The photograph is a close-up of the affected area. Reported duration is about one day. The lesion is associated with itching. The patient considered this a rash. The front of the torso is involved. The contributor notes the lesion is raised or bumpy.
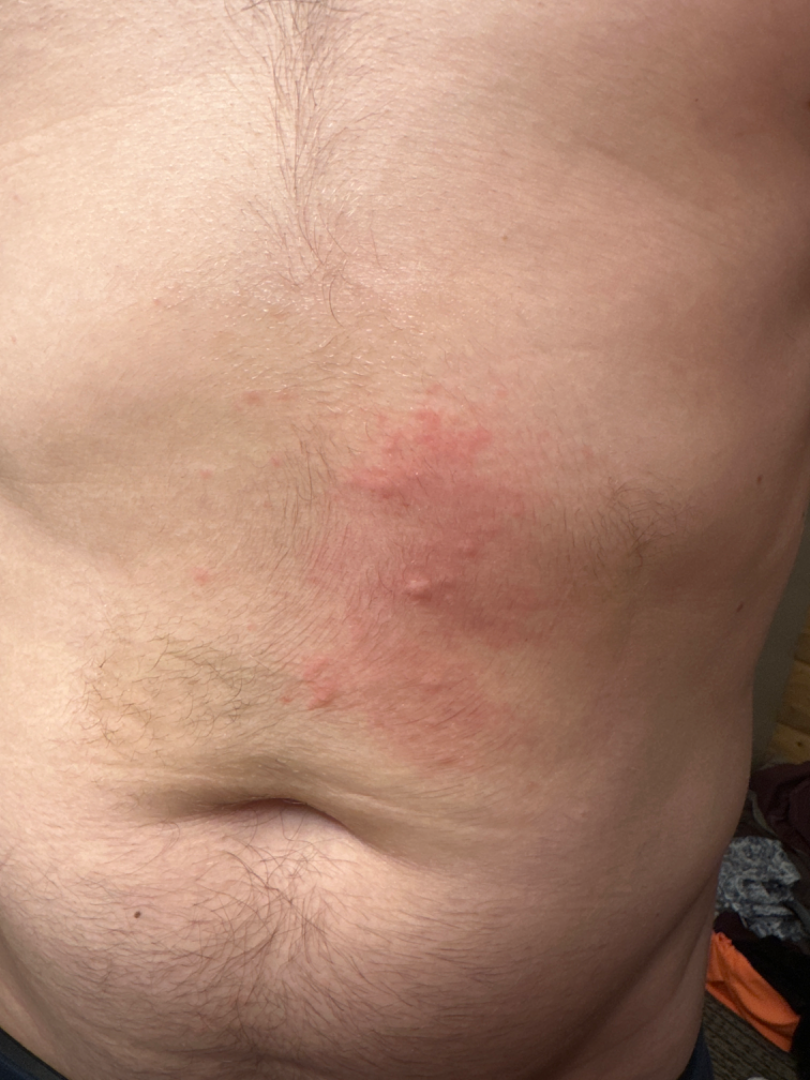Assessment:
On photographic review by a dermatologist: Urticaria (67%); Acute dermatitis, NOS (33%).